The photo was captured at an angle.
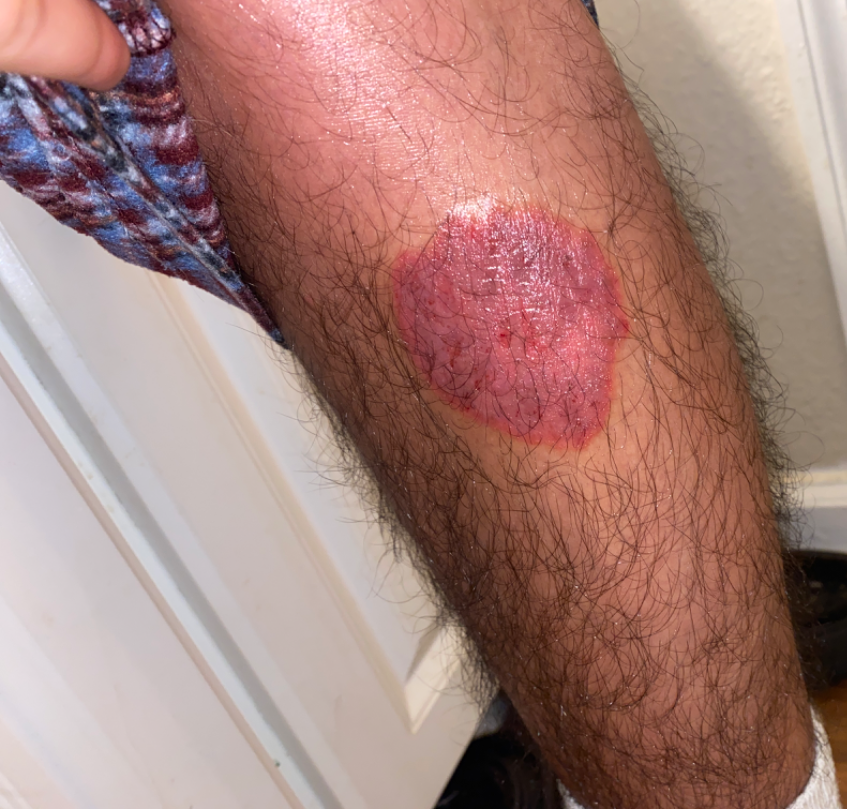assessment: unable to determine.